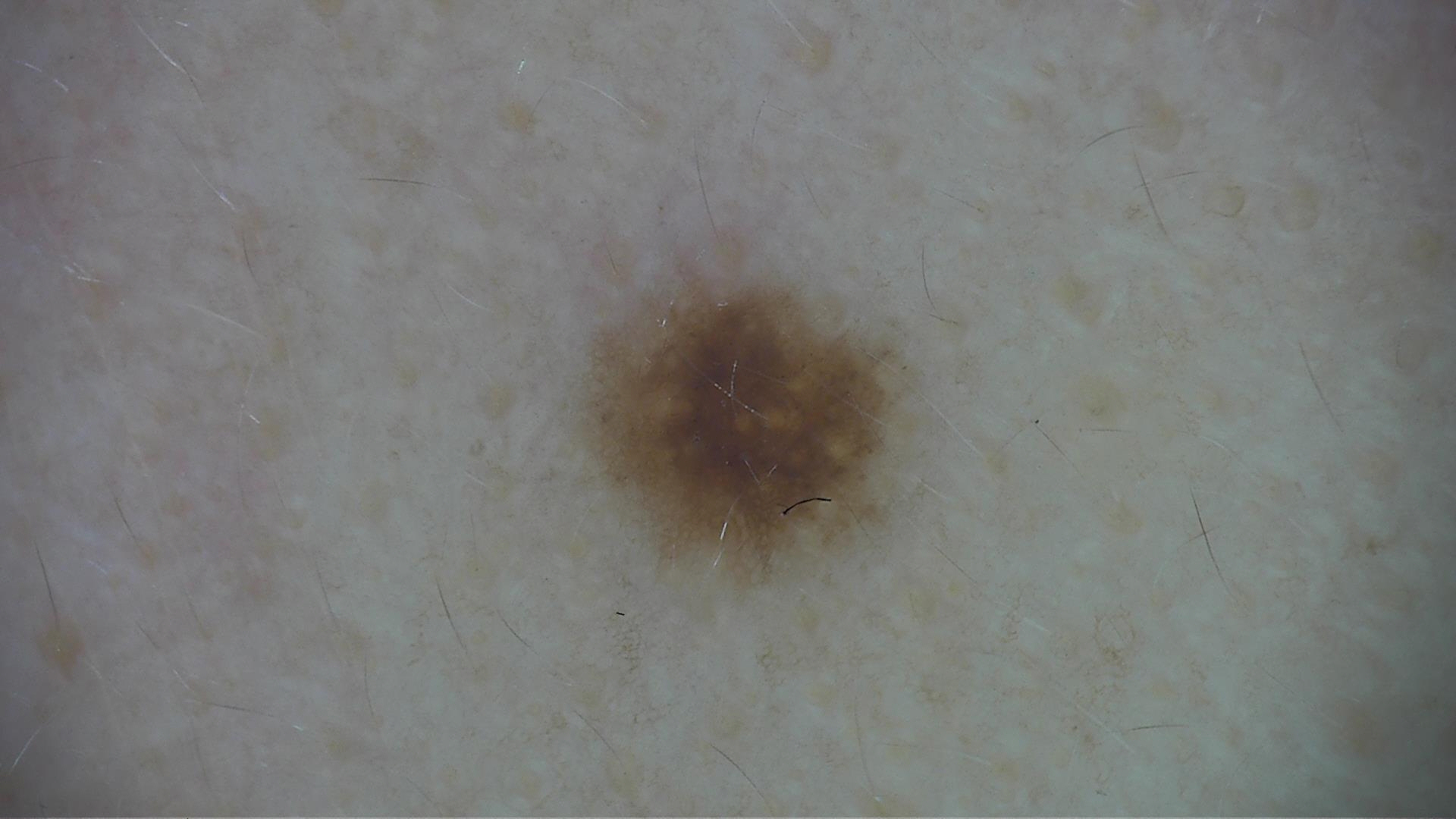Labeled as a Miescher nevus.